A dermatoscopic image of a skin lesion. A female subject aged 38-42.
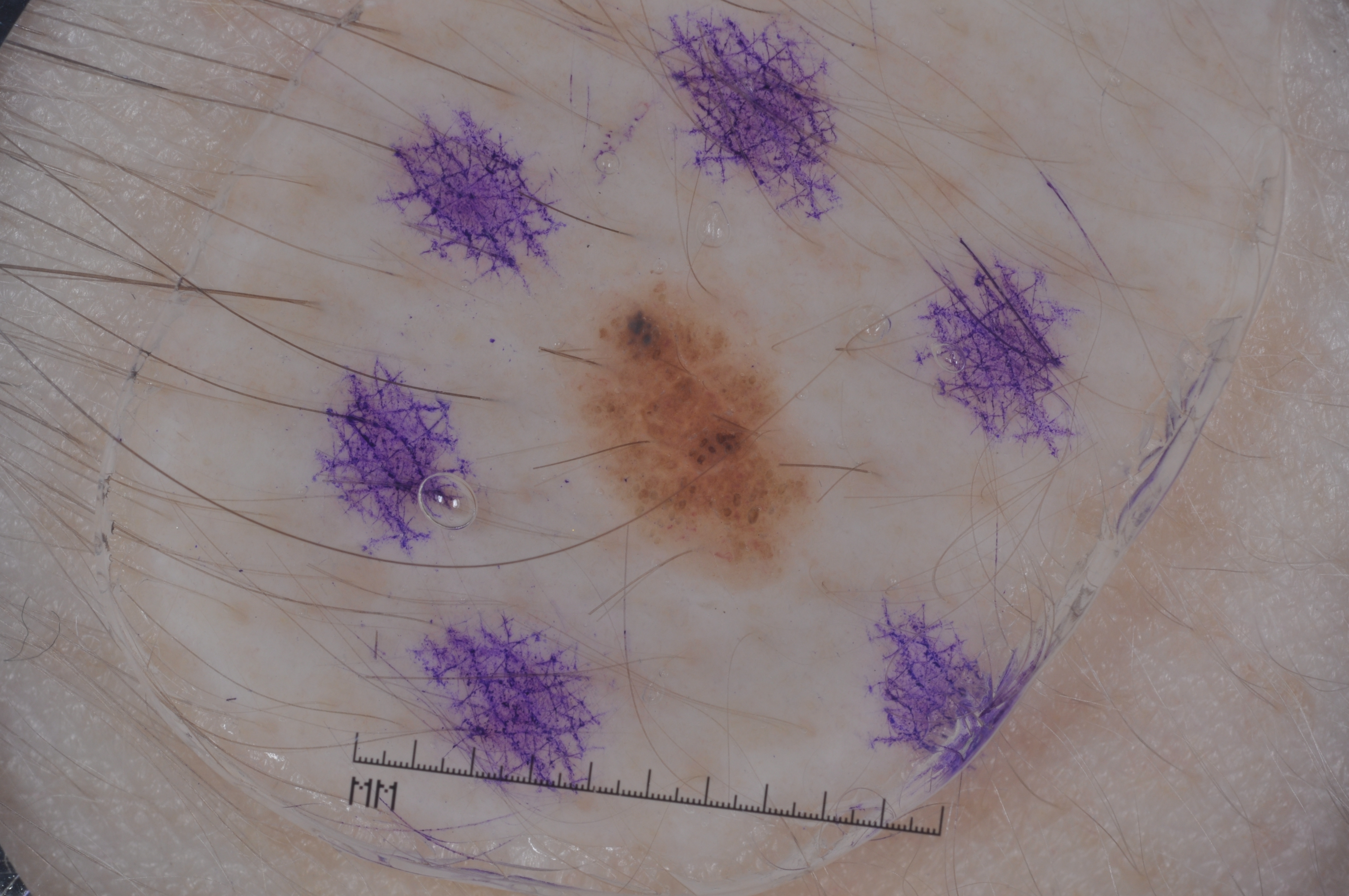lesion location = x1=545, y1=265, x2=830, y2=596; lesion extent = ~6% of the field; absent dermoscopic features = streaks, milia-like cysts, negative network, and pigment network; diagnosis = a melanocytic nevus, a benign skin lesion.